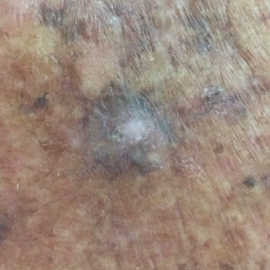Summary: A male subject 76 years old. Recorded as Fitzpatrick phototype III. By history, prior skin cancer (patient or family), no prior malignancy (patient or family), and no pesticide exposure. The lesion is roughly 9 by 7 mm. Per patient report, the lesion itches. Pathology: The biopsy diagnosis was a malignant skin lesion — a squamous cell carcinoma.